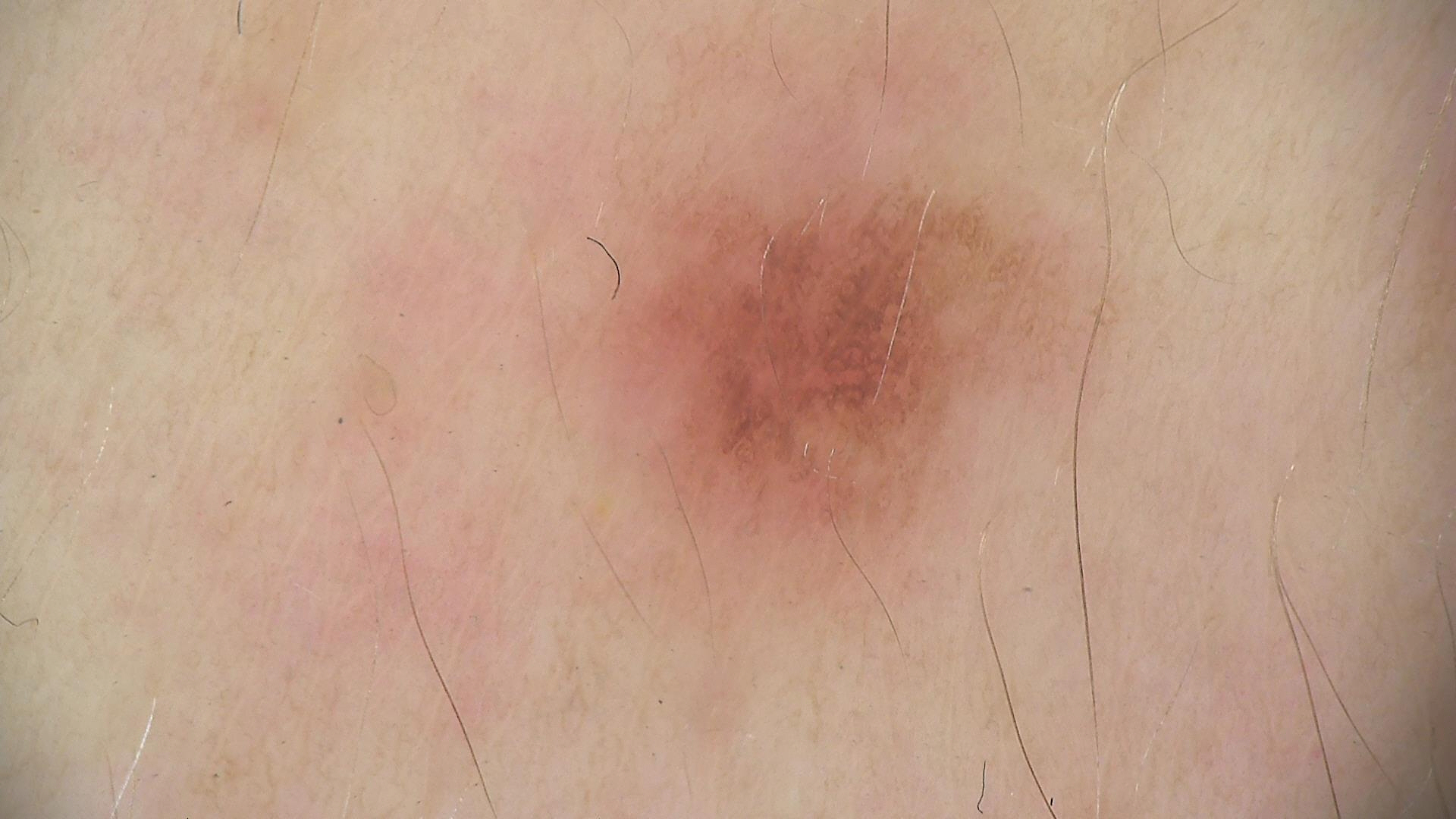Impression:
The diagnostic label was a benign lesion — a dysplastic junctional nevus.